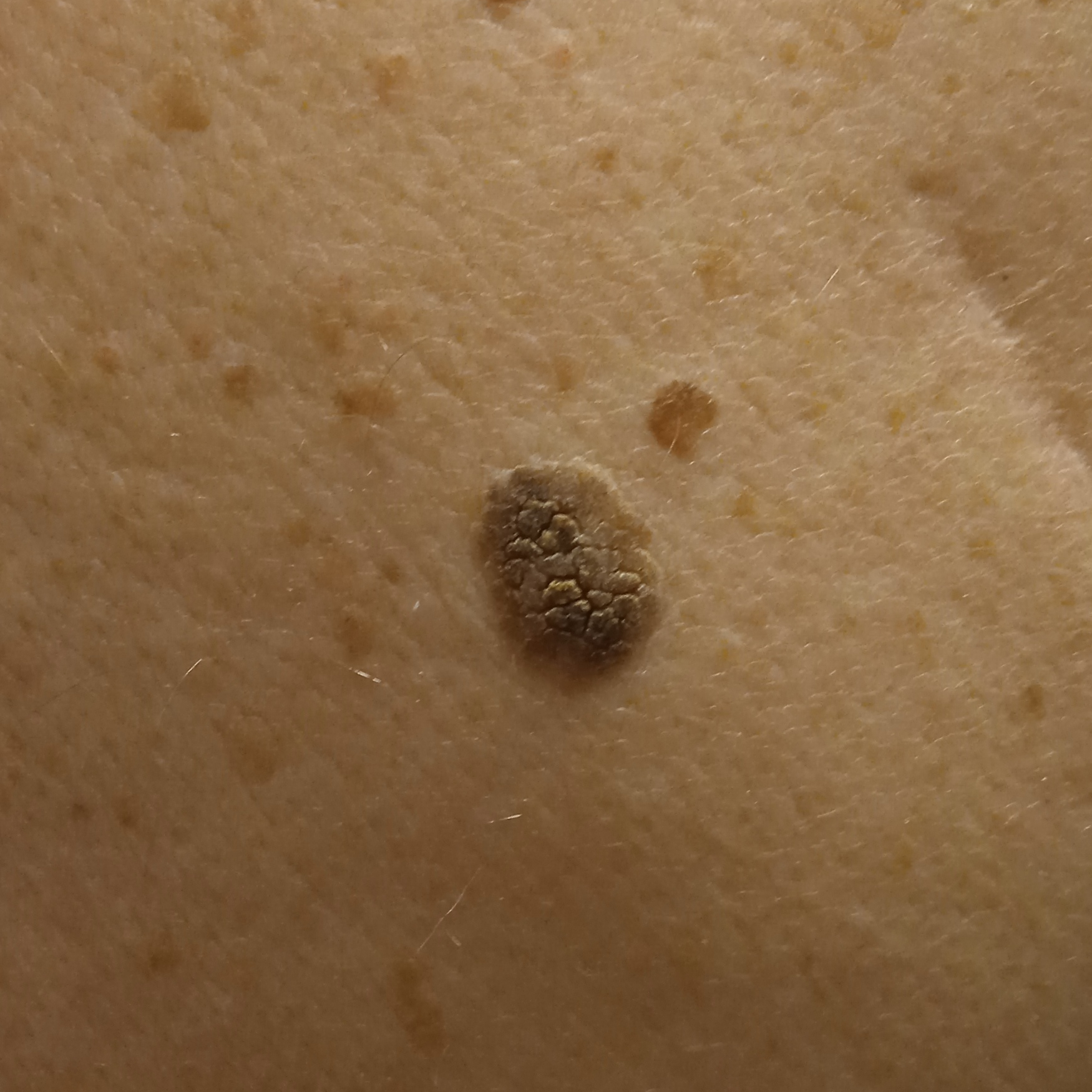A macroscopic clinical photograph of a skin lesion. A male patient age 78. Acquired for a research image collection, with no referral diagnosis. The lesion involves the back. Measuring roughly 15.1 mm. The consensus diagnosis for this lesion was a seborrheic keratosis.